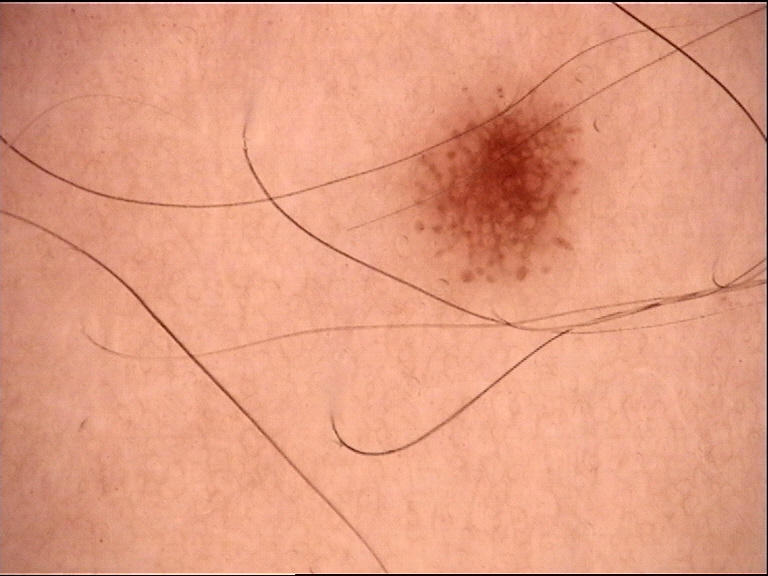{"diagnosis": {"name": "dysplastic junctional nevus", "code": "jd", "malignancy": "benign", "super_class": "melanocytic", "confirmation": "expert consensus"}}